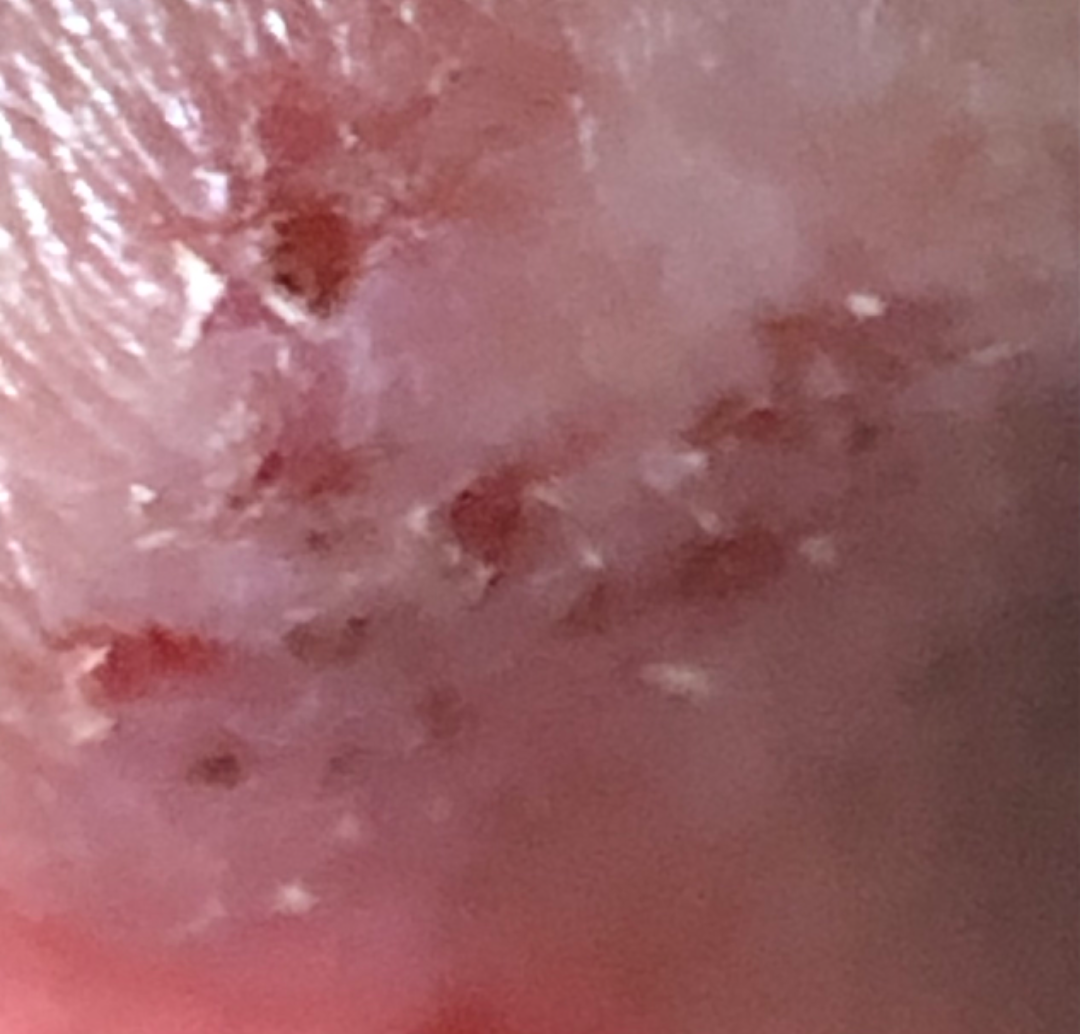Assessment:
The skin findings could not be characterized from the image.
Clinical context:
Present for more than five years. The patient is 60–69, female. Skin tone: self-reported Fitzpatrick skin type III. The patient described the issue as a rash. Close-up view. Reported lesion symptoms include pain, bothersome appearance and enlargement. The front of the torso, head or neck, back of the torso and arm are involved. The lesion is described as rough or flaky and raised or bumpy.